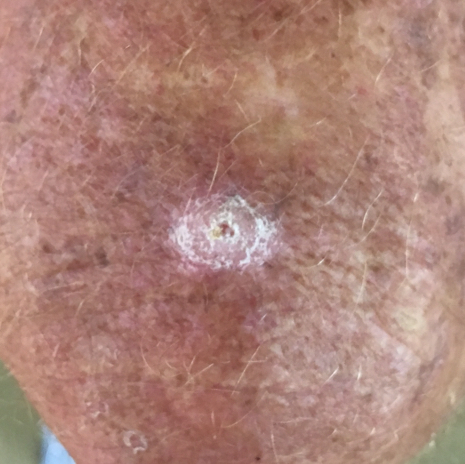Clinical context:
A clinical photograph showing a skin lesion. A patient aged 73. The lesion was found on a thigh. By the patient's account, the lesion itches.
Impression:
Consistent with an actinic keratosis.